This is a close-up image: 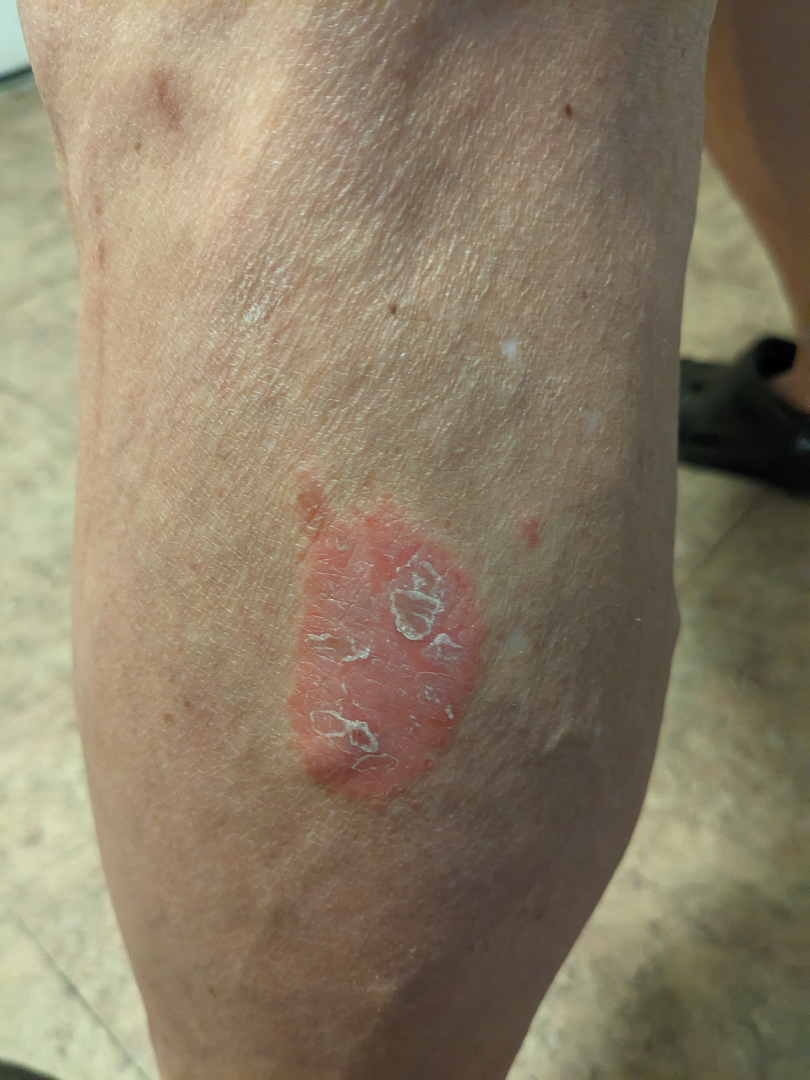Notes:
– differential — single-reviewer assessment: the leading consideration is Psoriasis; also raised was Parapsoriasis; an alternative is Psoriasiform dermatitis